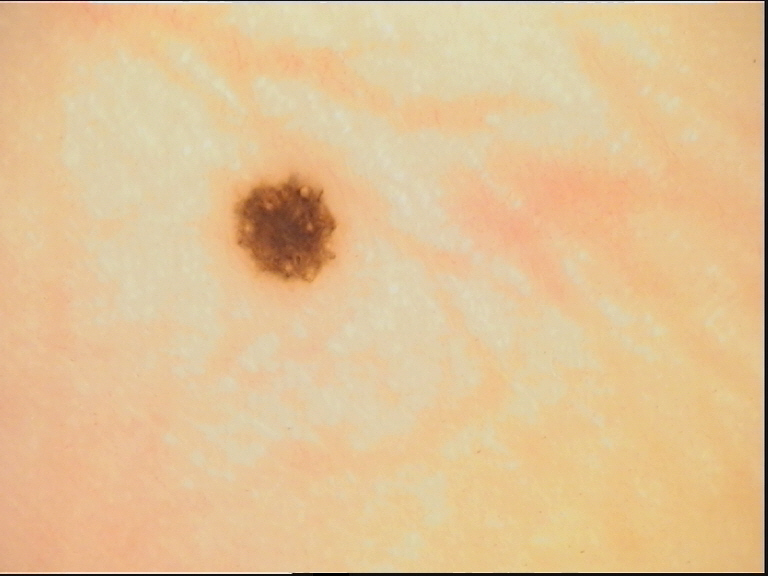  image: dermoscopy
  diagnosis:
    name: acral dysplastic junctional nevus
    code: ajd
    malignancy: benign
    super_class: melanocytic
    confirmation: expert consensus